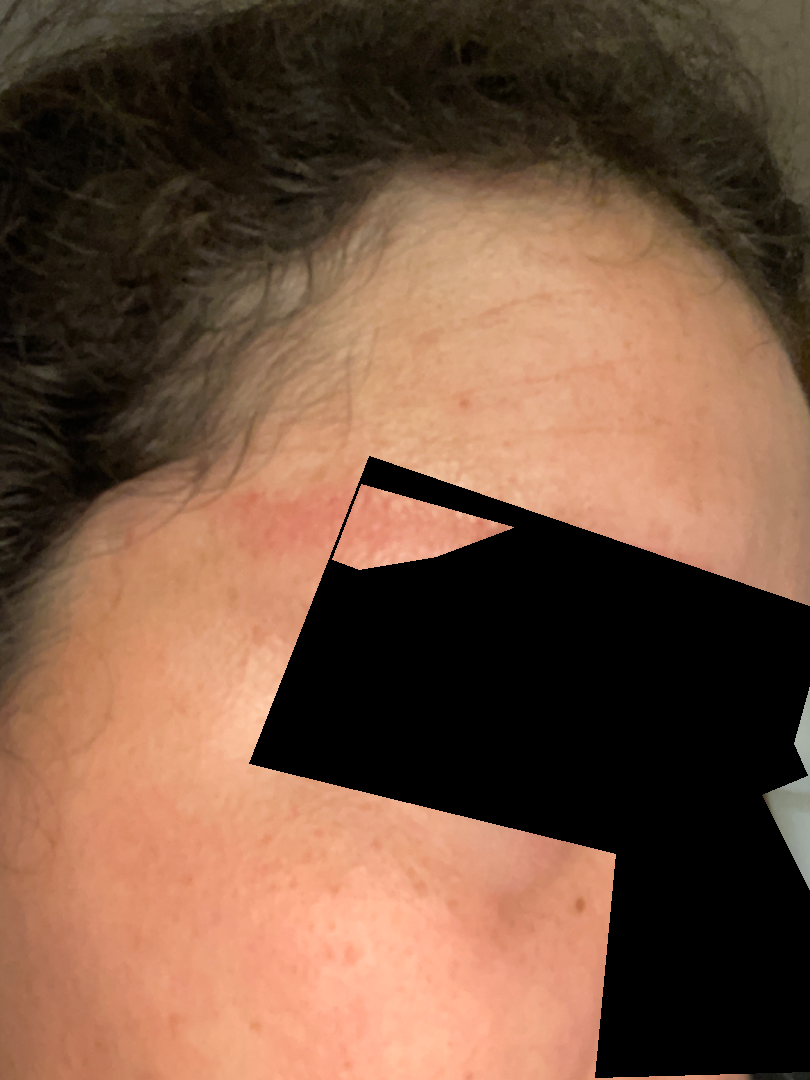Impression: Diagnostic features were not clearly distinguishable in this photograph.